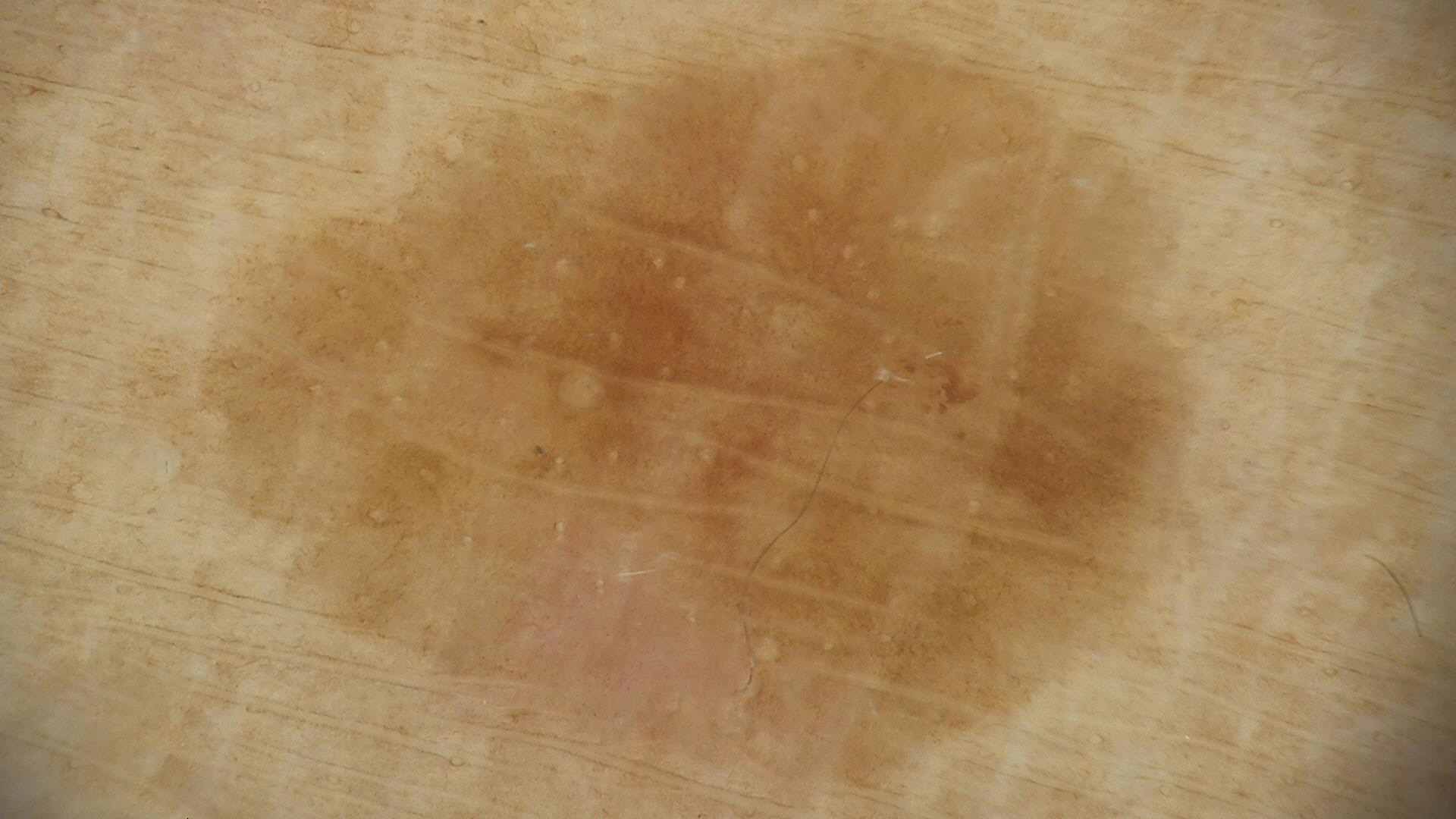  image: dermoscopy
  diagnosis:
    name: seborrheic keratosis
    code: sk
    malignancy: benign
    super_class: non-melanocytic
    confirmation: expert consensus